Close-up view — 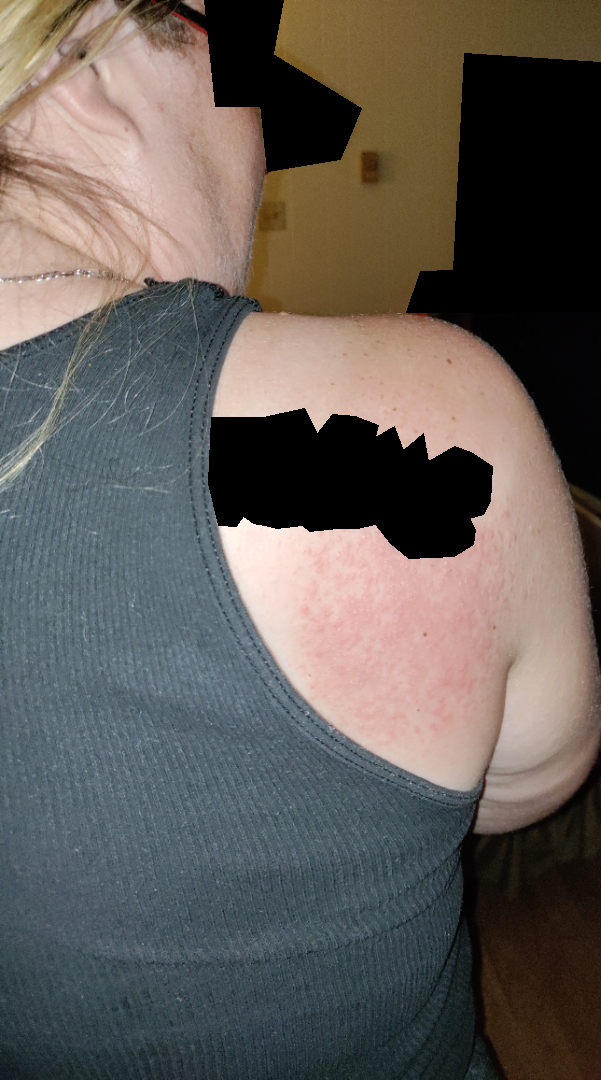assessment: not assessable.